A dermatoscopic image of a skin lesion; the patient is a female aged 33 to 37 — 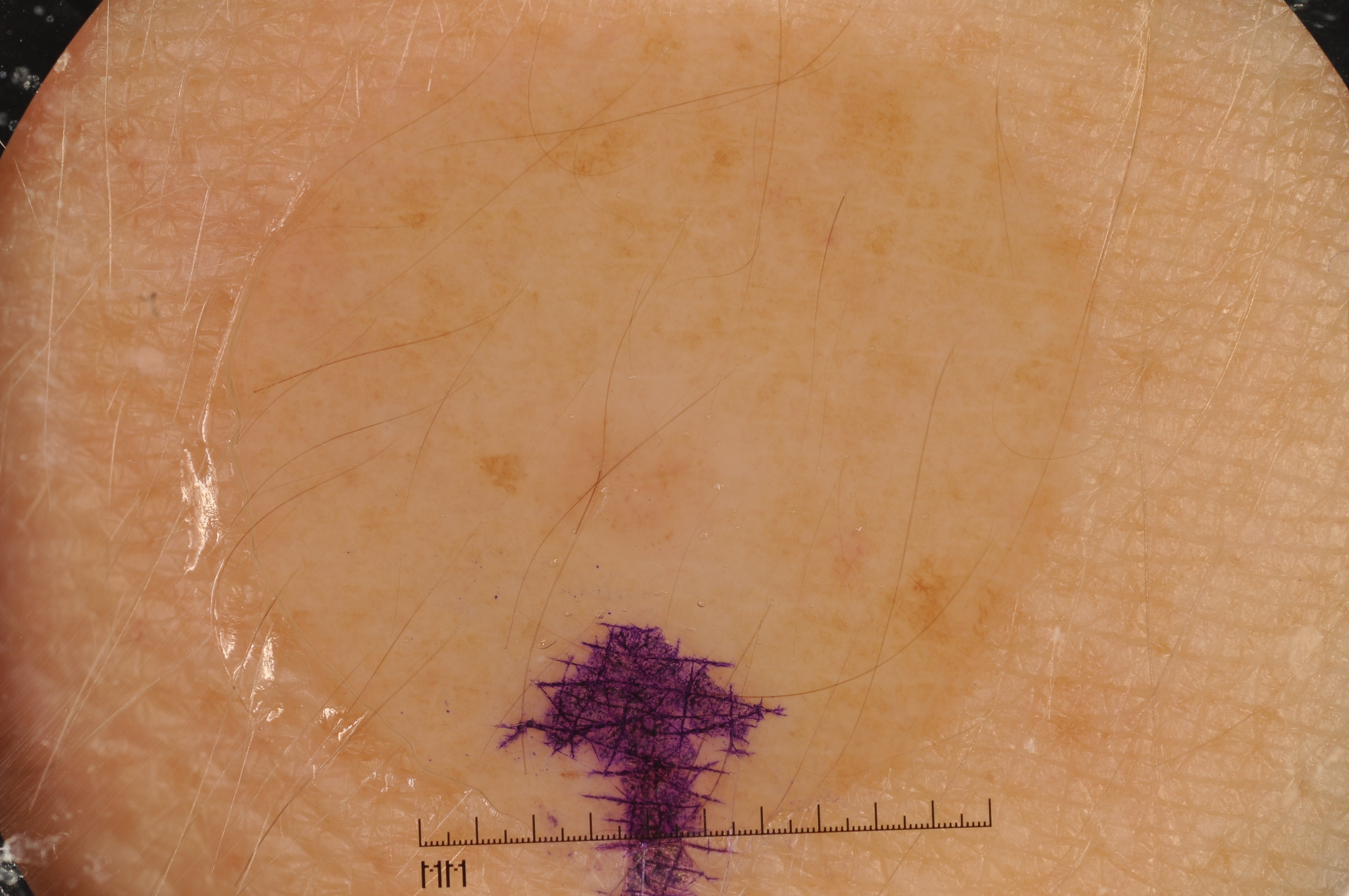Dermoscopy demonstrates milia-like cysts, with no negative network, streaks, or pigment network.
In (x1, y1, x2, y2) order, the lesion is located at <box>520, 379, 734, 571</box>.
Diagnosed as a melanocytic nevus, a benign lesion.